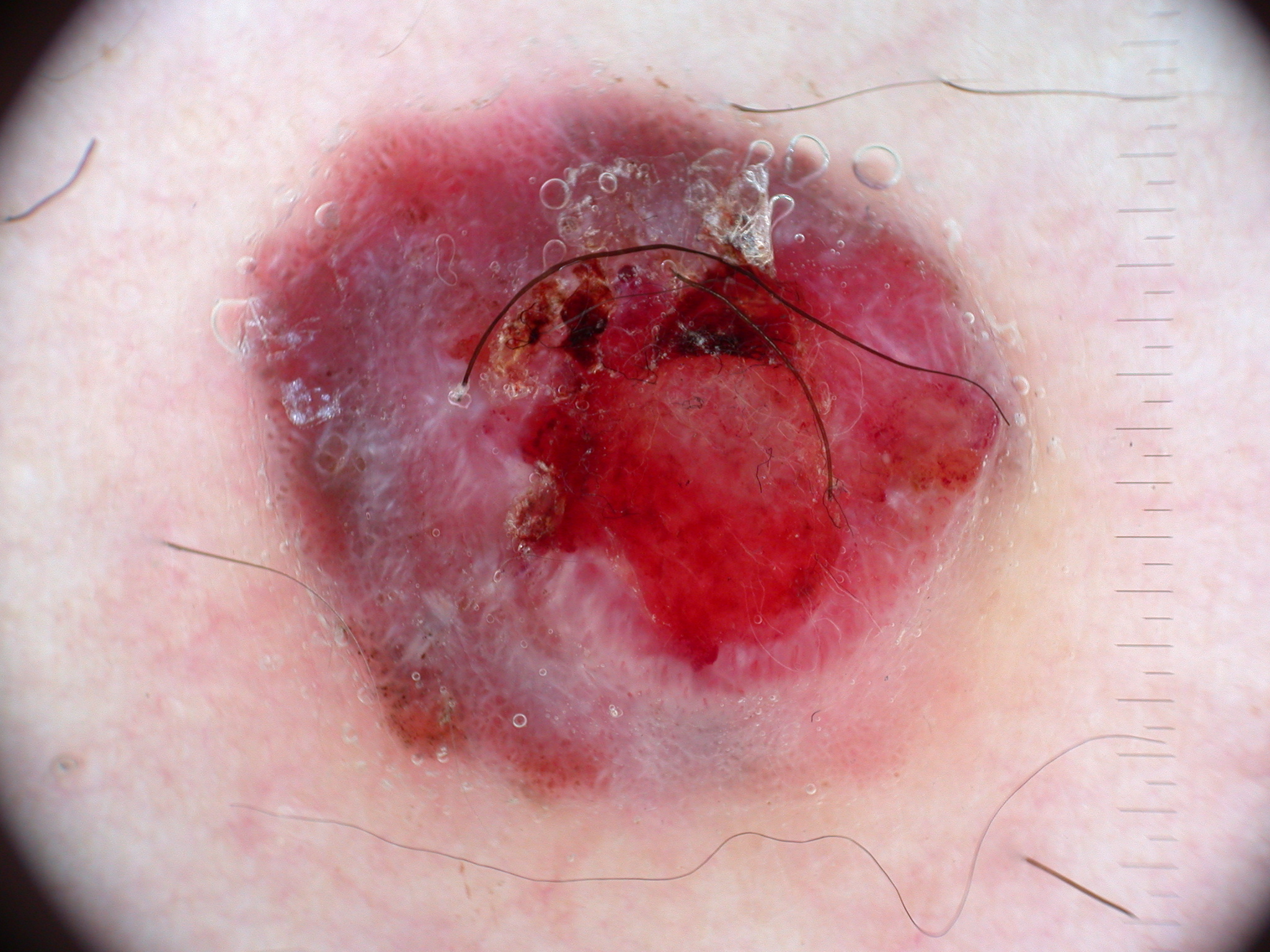Dermoscopy of a skin lesion. The visible lesion spans bbox(240, 82, 1023, 821). Dermoscopy demonstrates negative network. On biopsy, the diagnosis was a melanoma.